A skin lesion imaged with a dermatoscope.
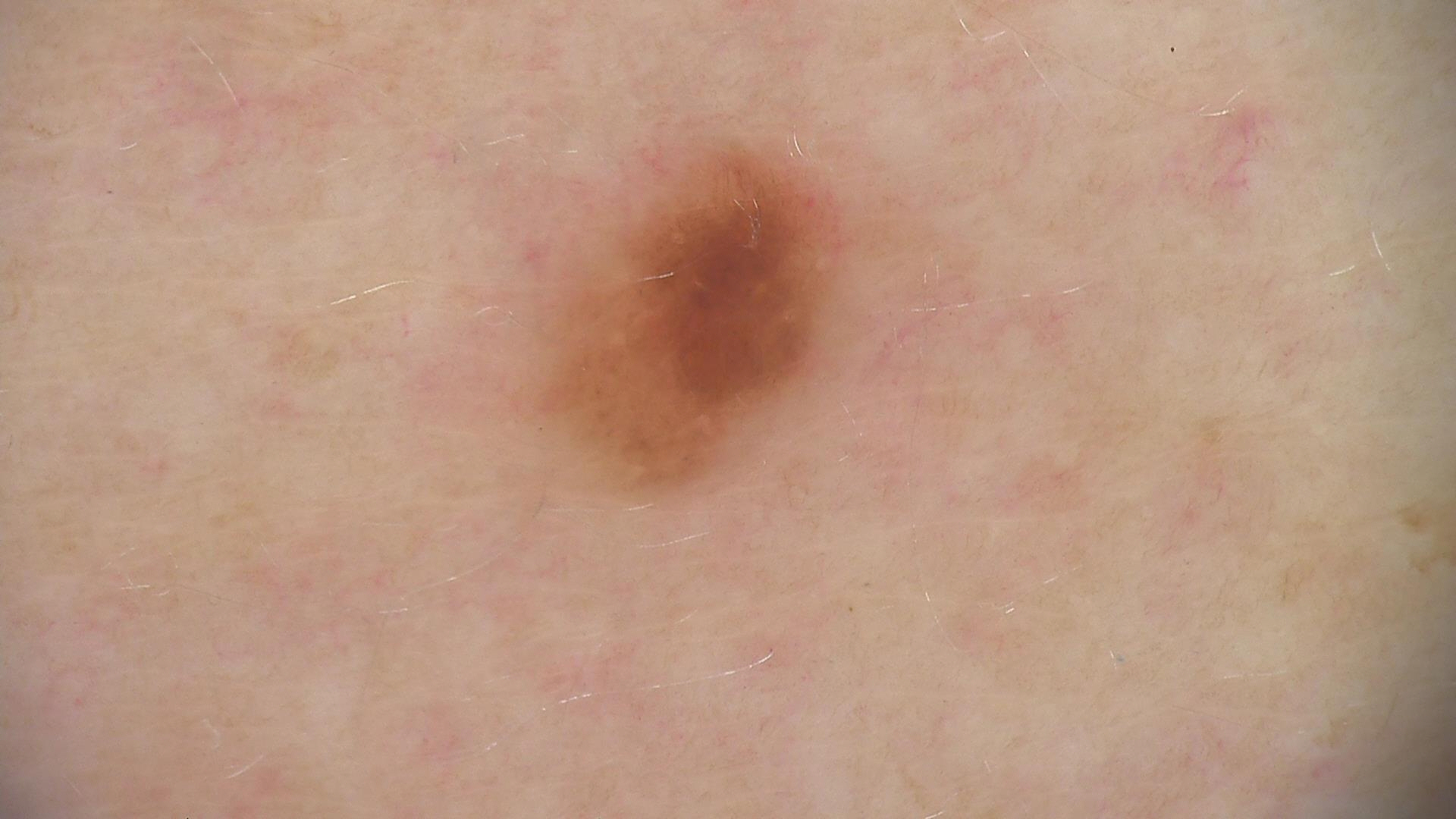Conclusion: Classified as a dysplastic junctional nevus.